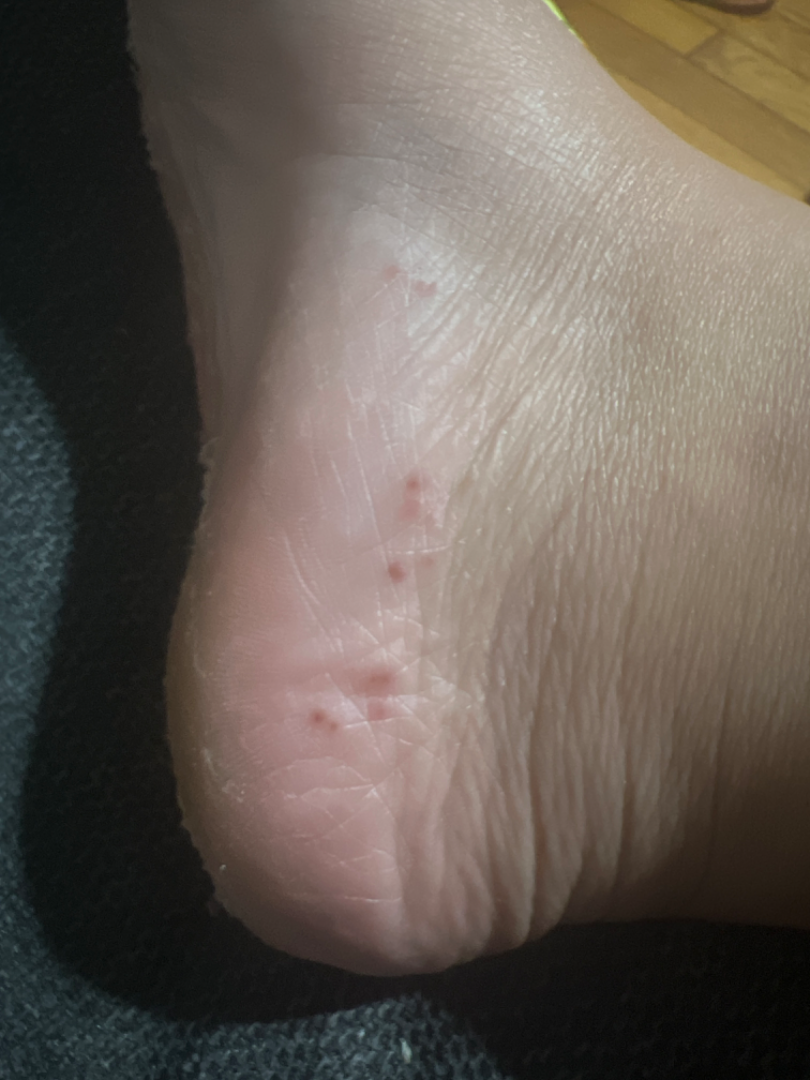surface texture — raised or bumpy | symptoms — itching | self-categorized as — skin that appeared healthy to them | patient — female, age 18–29 | shot type — close-up | skin tone — FST II | present for — one to four weeks | body site — top or side of the foot | diagnostic considerations — favoring Tinea; also consider Eczema.